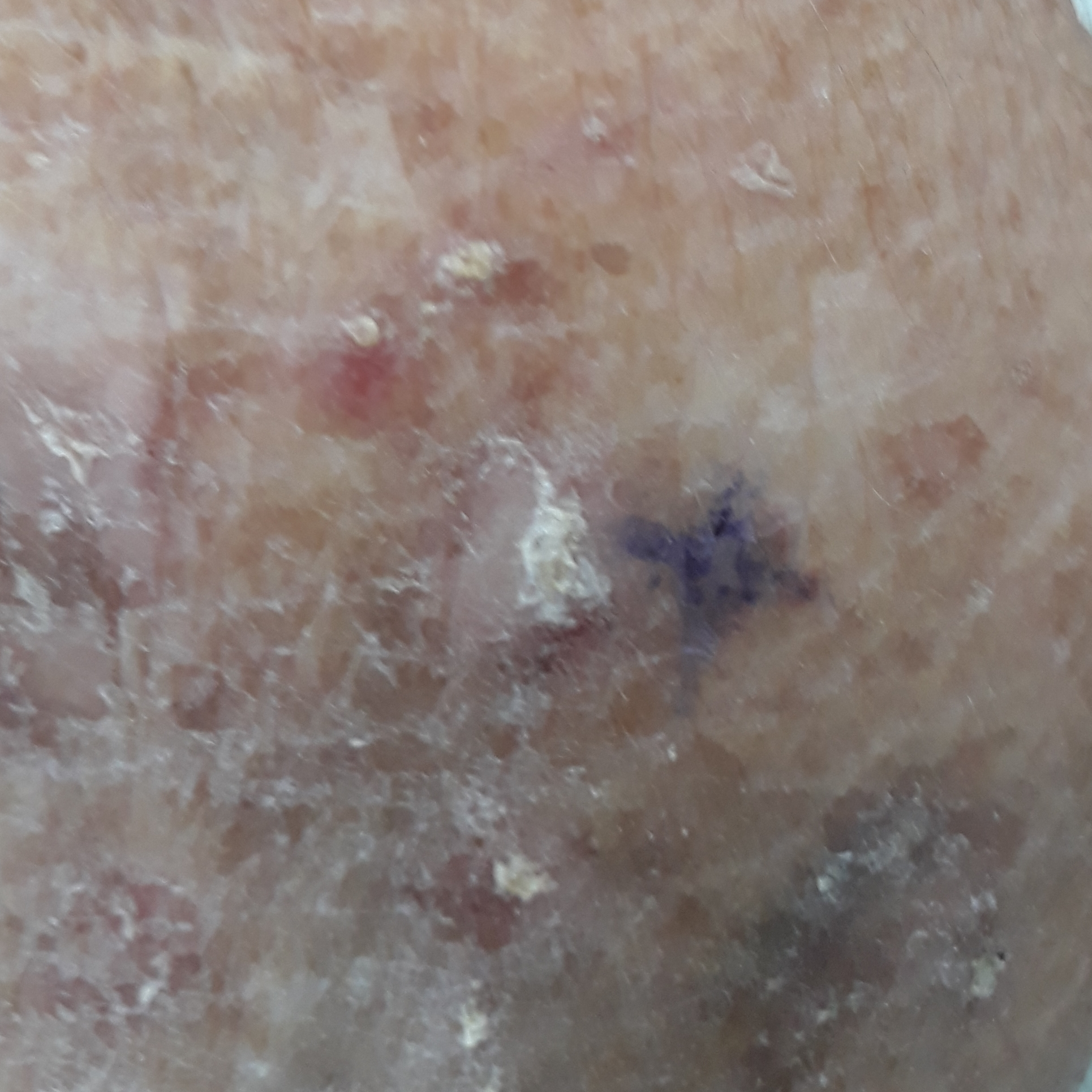The patient is FST III.
A clinical photograph of a skin lesion.
A female subject in their 60s.
History notes pesticide exposure and no alcohol use.
The lesion involves a hand.
The lesion measures 5 × 4 mm.
The patient describes that the lesion hurts, itches, and is elevated, but has not bled.
Histopathology confirmed a squamous cell carcinoma.